The photo was captured at a distance; located on the leg; the patient is 18–29, female:
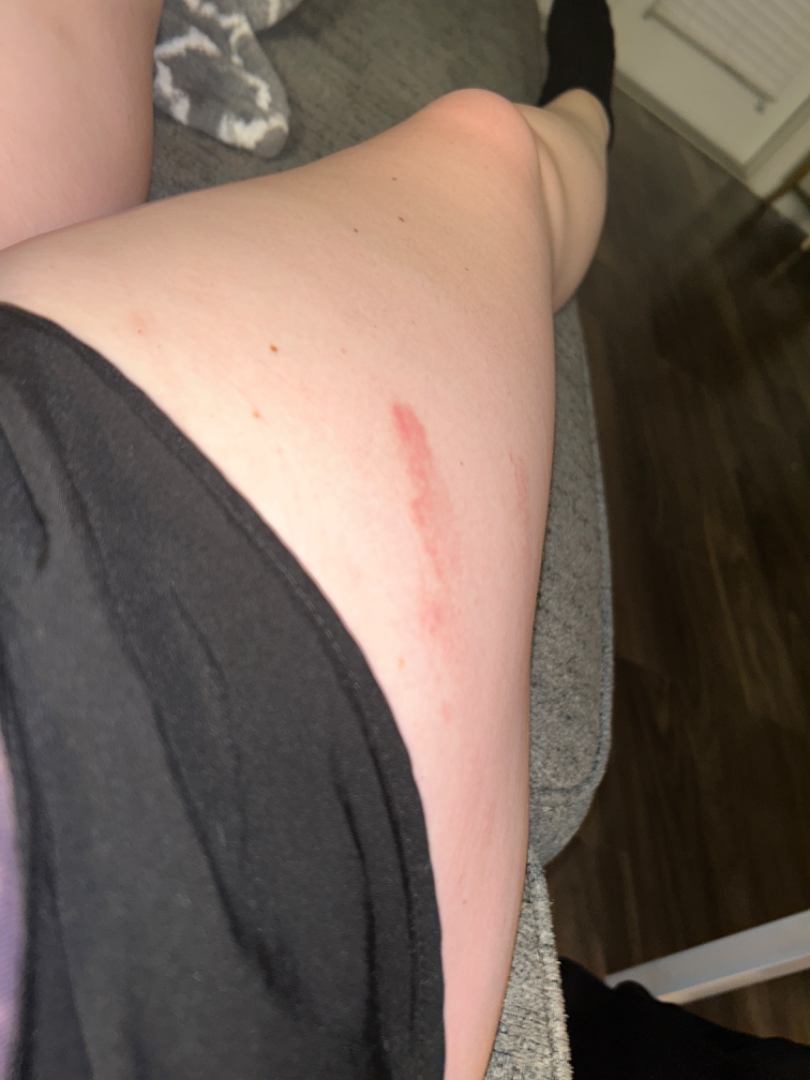The case was difficult to assess from the available photograph. Skin tone: lay reviewers estimated Monk Skin Tone 2 or 3. The contributor reports the condition has been present for less than one week. The contributor reports the lesion is raised or bumpy and flat. The patient did not report lesion symptoms. The patient considered this a rash.